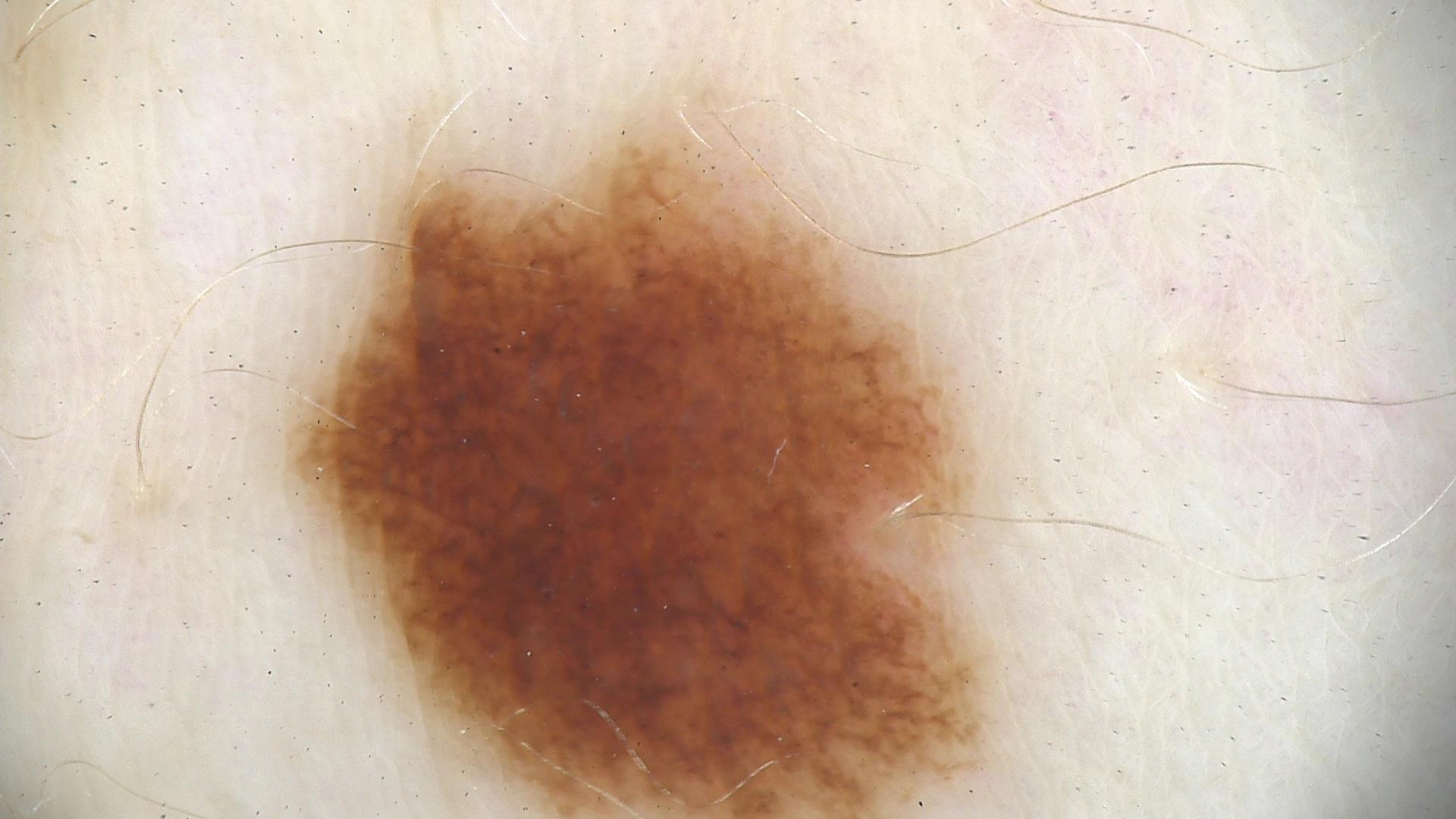Labeled as a dysplastic junctional nevus.